Dermoscopy of a skin lesion: 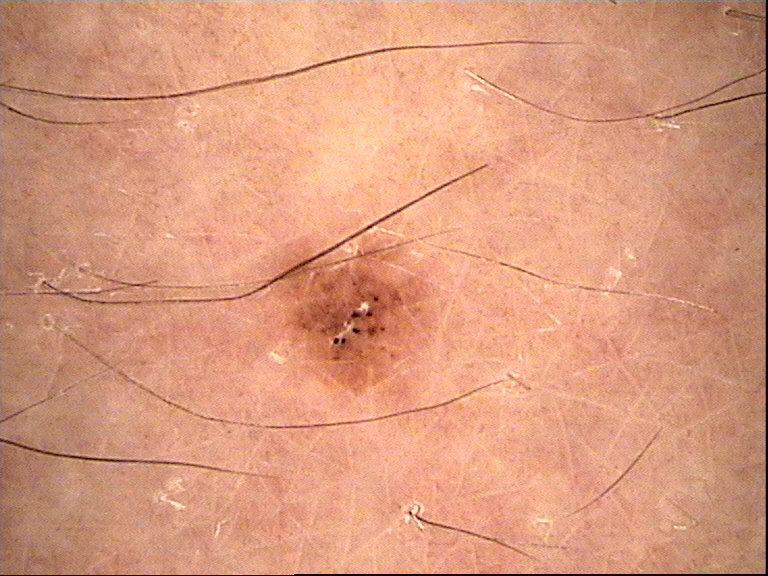<lesion>
<diagnosis>
<name>dysplastic junctional nevus</name>
<code>jd</code>
<malignancy>benign</malignancy>
<super_class>melanocytic</super_class>
<confirmation>expert consensus</confirmation>
</diagnosis>
</lesion>